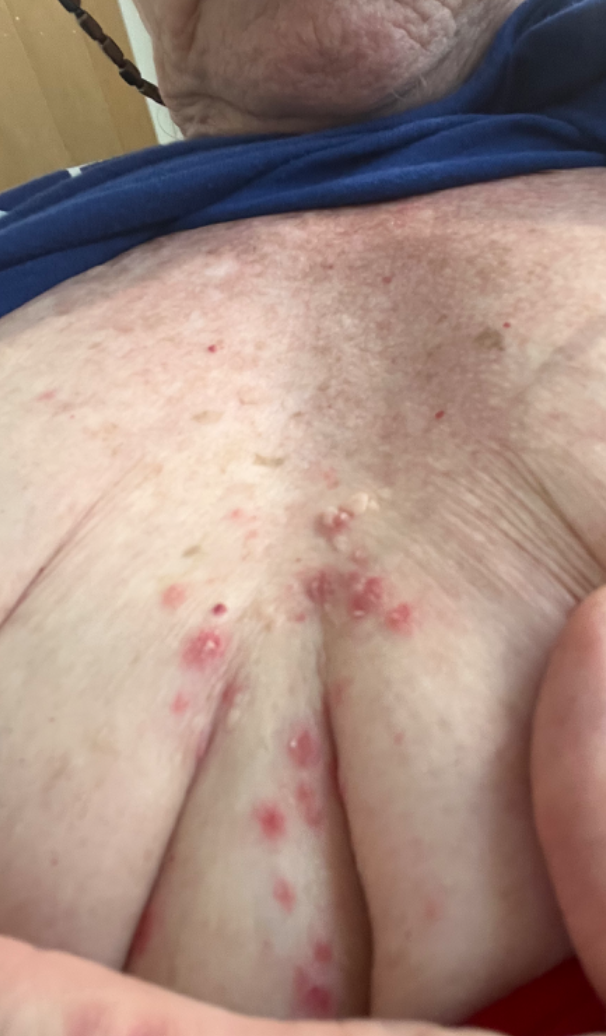Findings:
– photo taken · at an angle
– location · front of the torso
– subject · female, age 70–79
– clinical impression · most consistent with Grover's disease; with consideration of Folliculitis; less likely is Acne; less probable is Irritant Contact Dermatitis; lower on the differential is Pemphigus foliaceus; a more distant consideration is Seborrheic Dermatitis